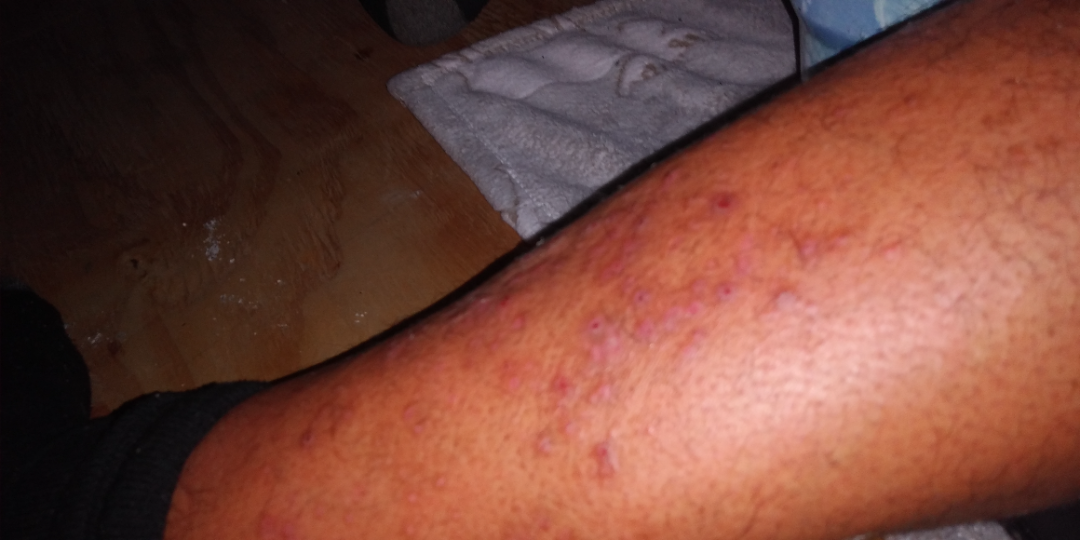On teledermatology review: Lichen planus/lichenoid eruption and Prurigo nodularis were each considered, in no particular order; less probable is Drug Rash.